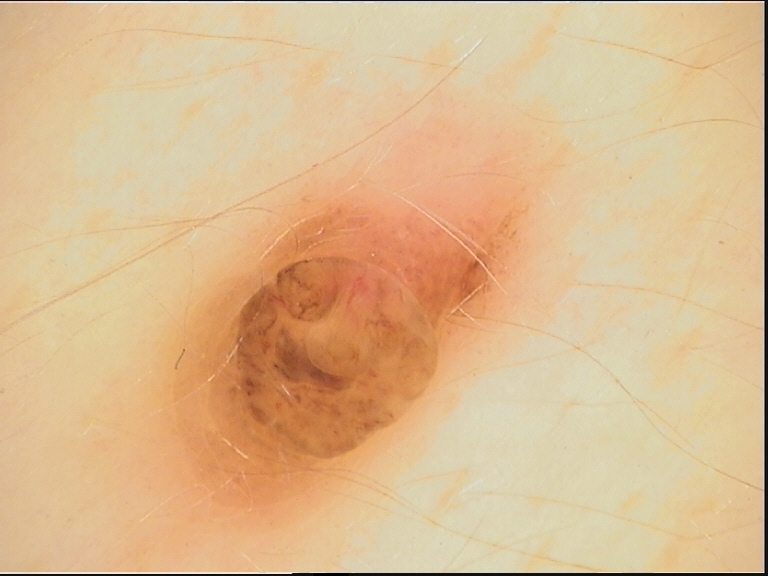The diagnosis was a dermal nevus.